This is a close-up image — 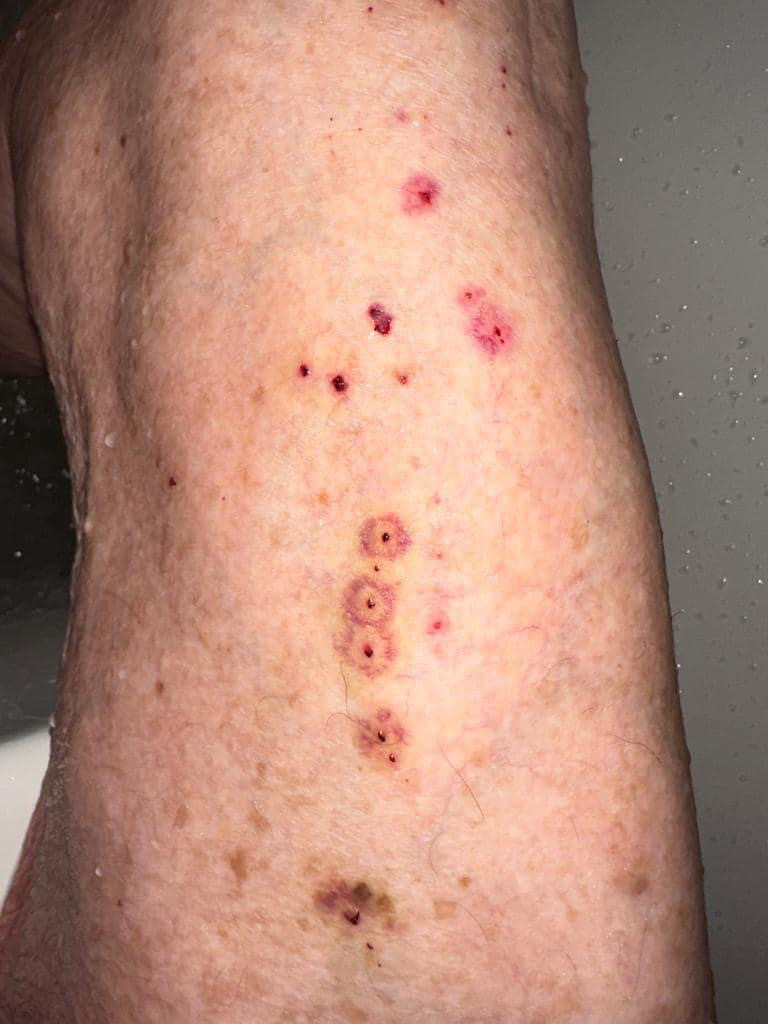{
  "differential": {
    "leading": [
      "Insect Bite"
    ],
    "considered": [
      "Erythema multiforme"
    ]
  }
}